Dermoscopy of a skin lesion.
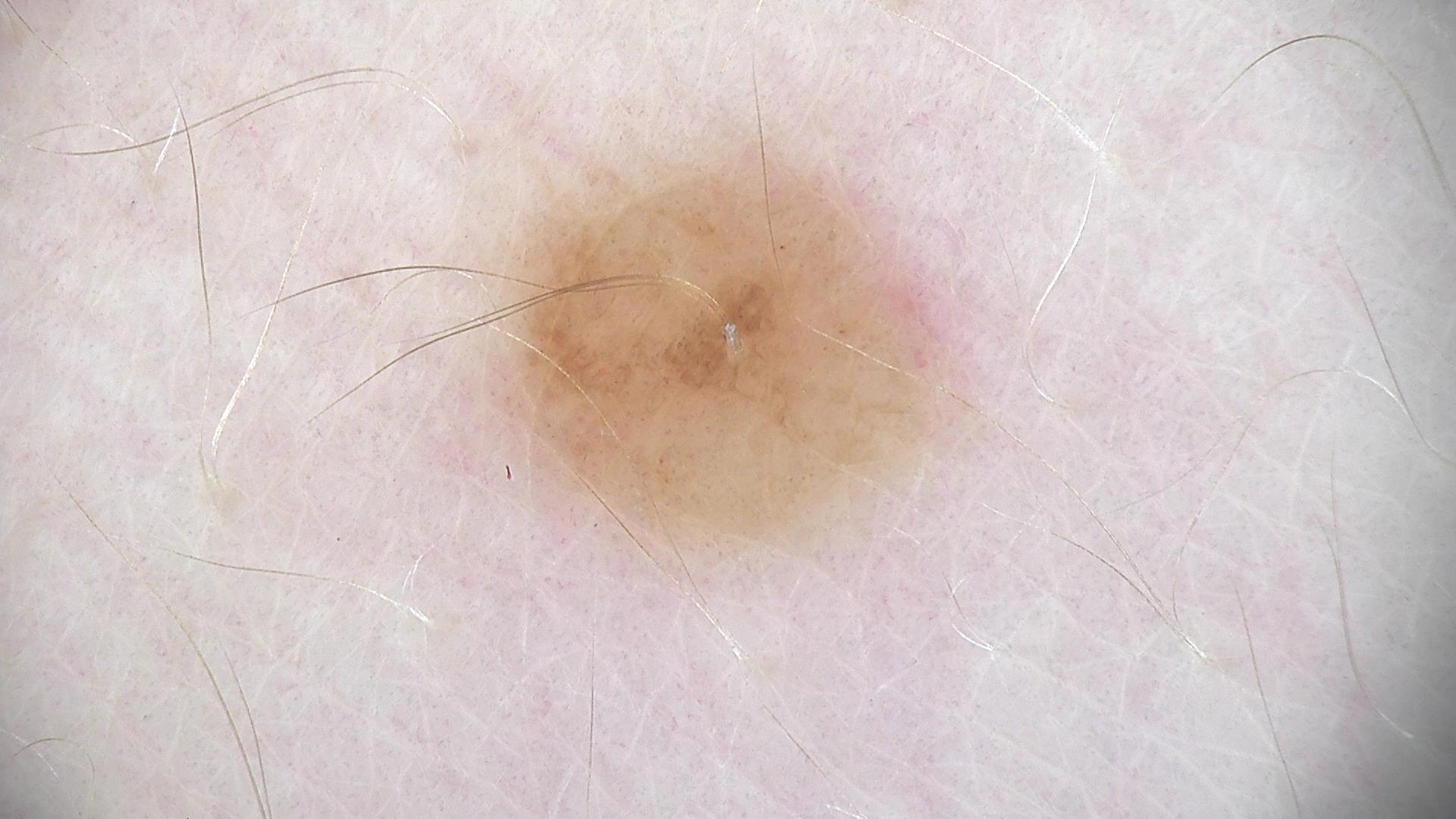Consistent with a banal lesion — a dermal nevus.